A skin lesion imaged with a dermatoscope:
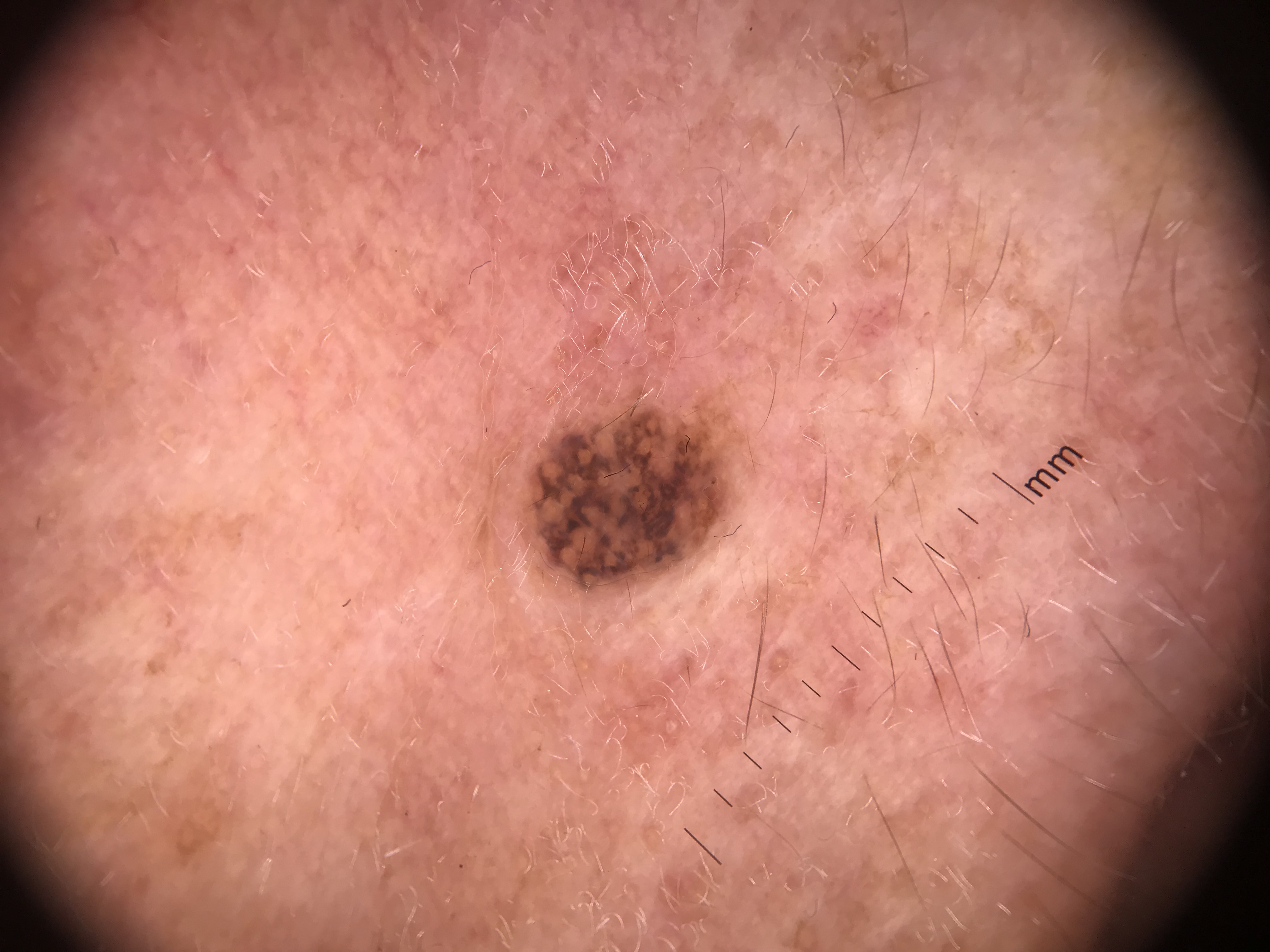Classified as a dysplastic junctional nevus.